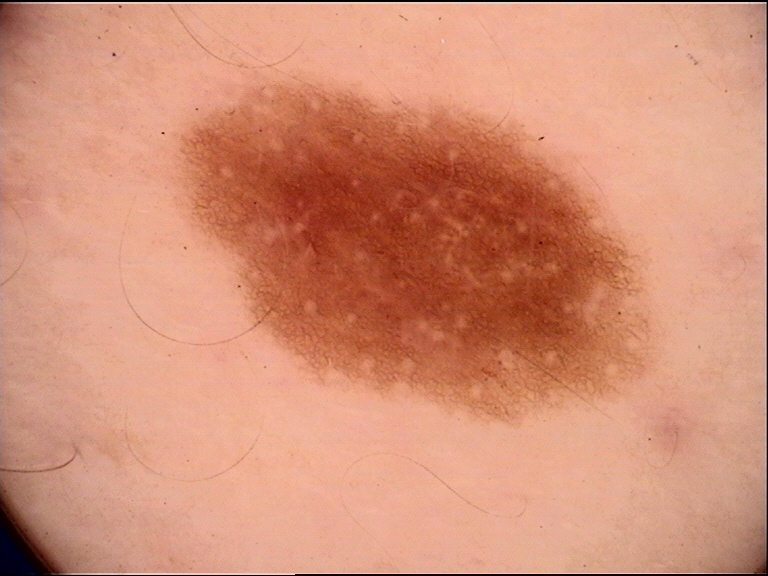modality = dermoscopy, diagnosis = dysplastic junctional nevus (expert consensus).